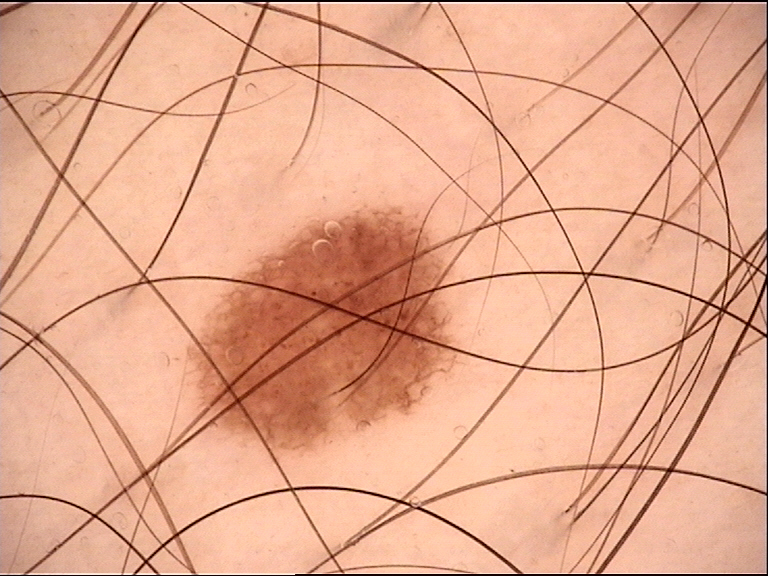A dermoscopic photograph of a skin lesion.
Consistent with a benign lesion — a dysplastic junctional nevus.